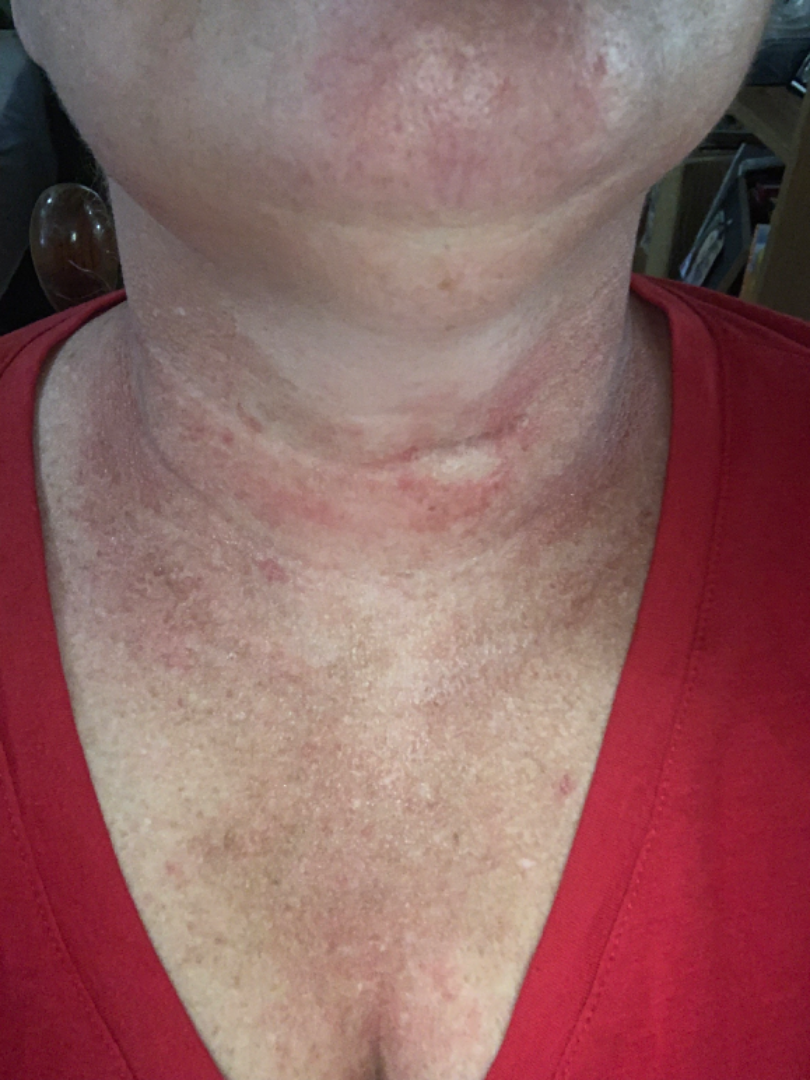The lesion involves the head or neck. The photograph is a close-up of the affected area. Photocontact dermatitis [berloque dermatitis] (possible); Allergic Contact Dermatitis (possible); Irritant Contact Dermatitis (possible).